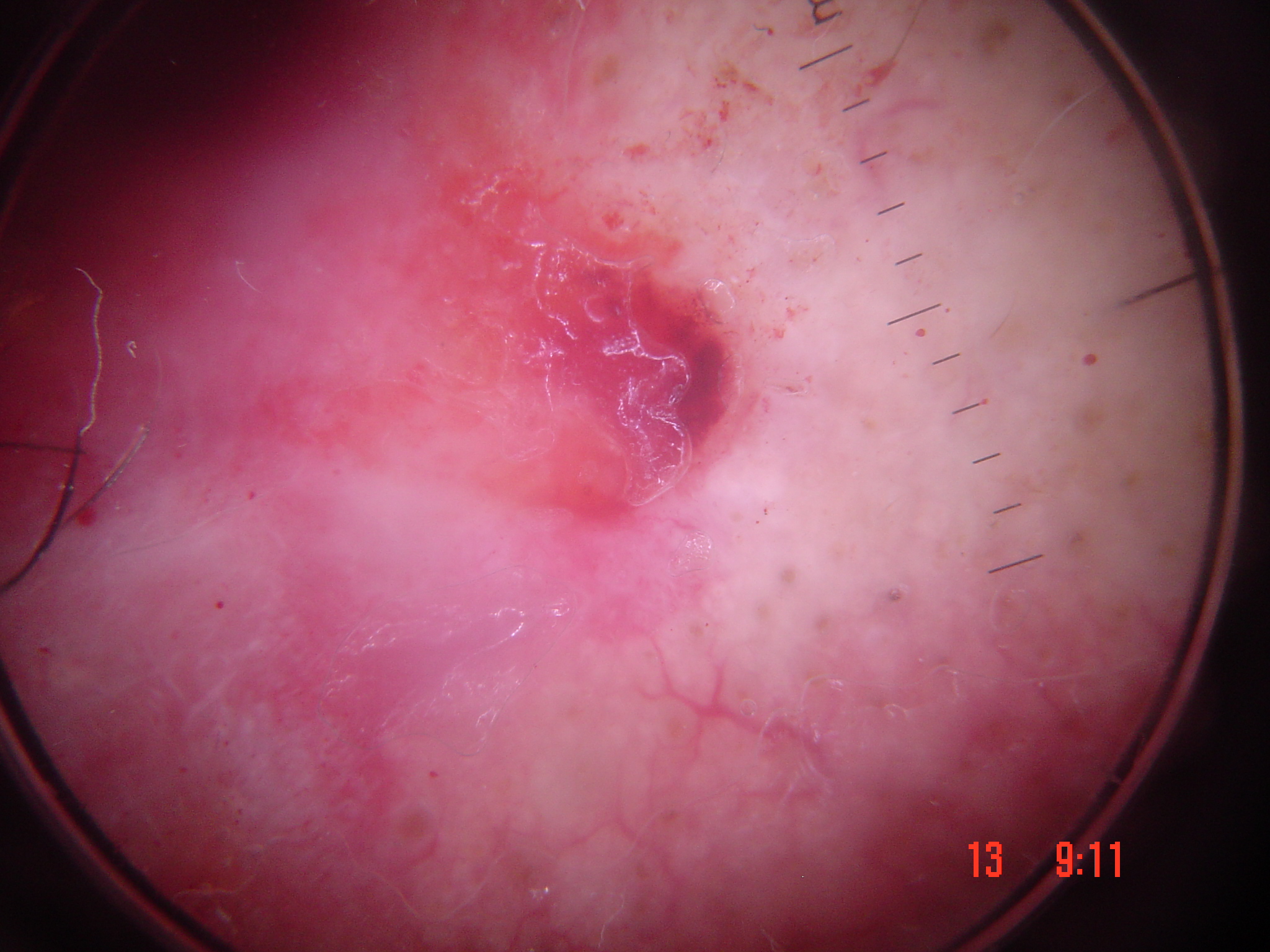Conclusion: Confirmed on histopathology as a squamous cell carcinoma.